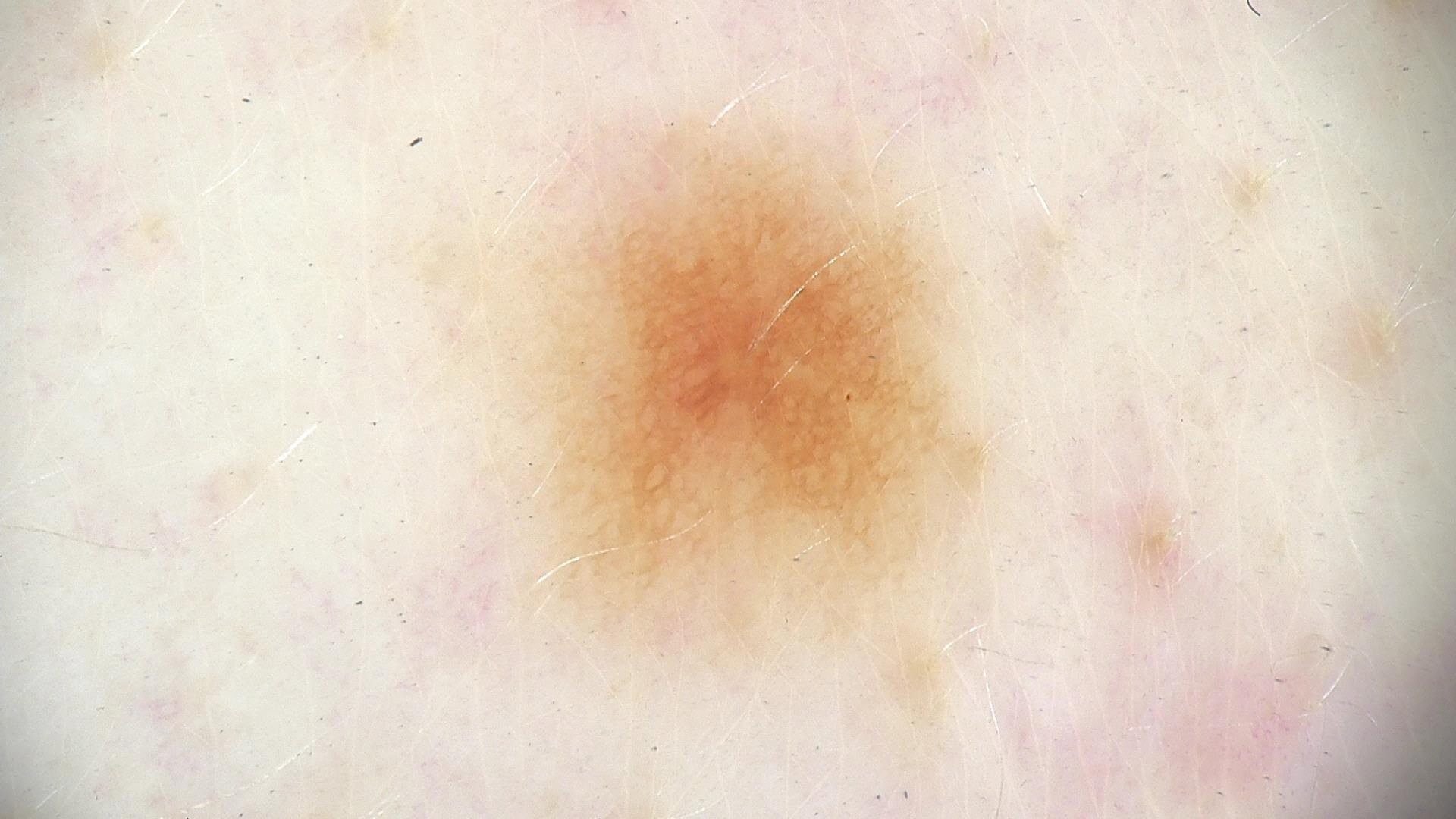Classified as a dysplastic junctional nevus.